A dermoscopic photograph of a skin lesion.
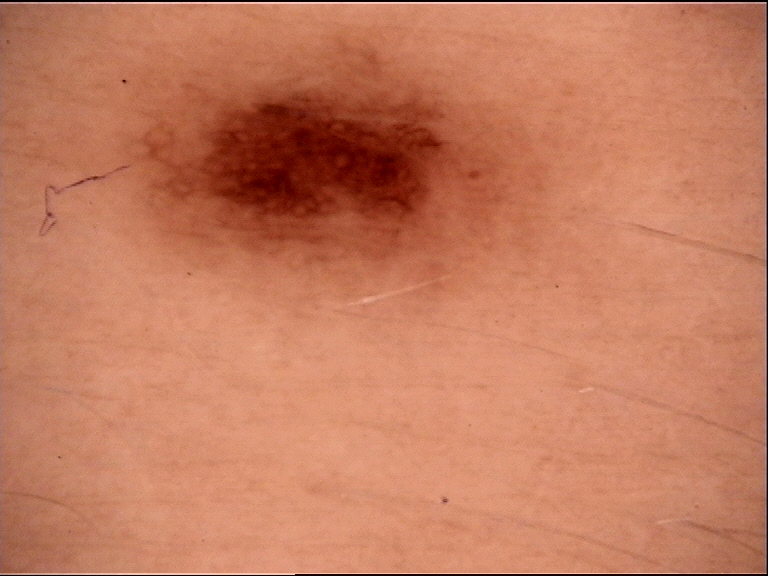assessment=dysplastic junctional nevus (expert consensus).